A dermoscopic image of a skin lesion — 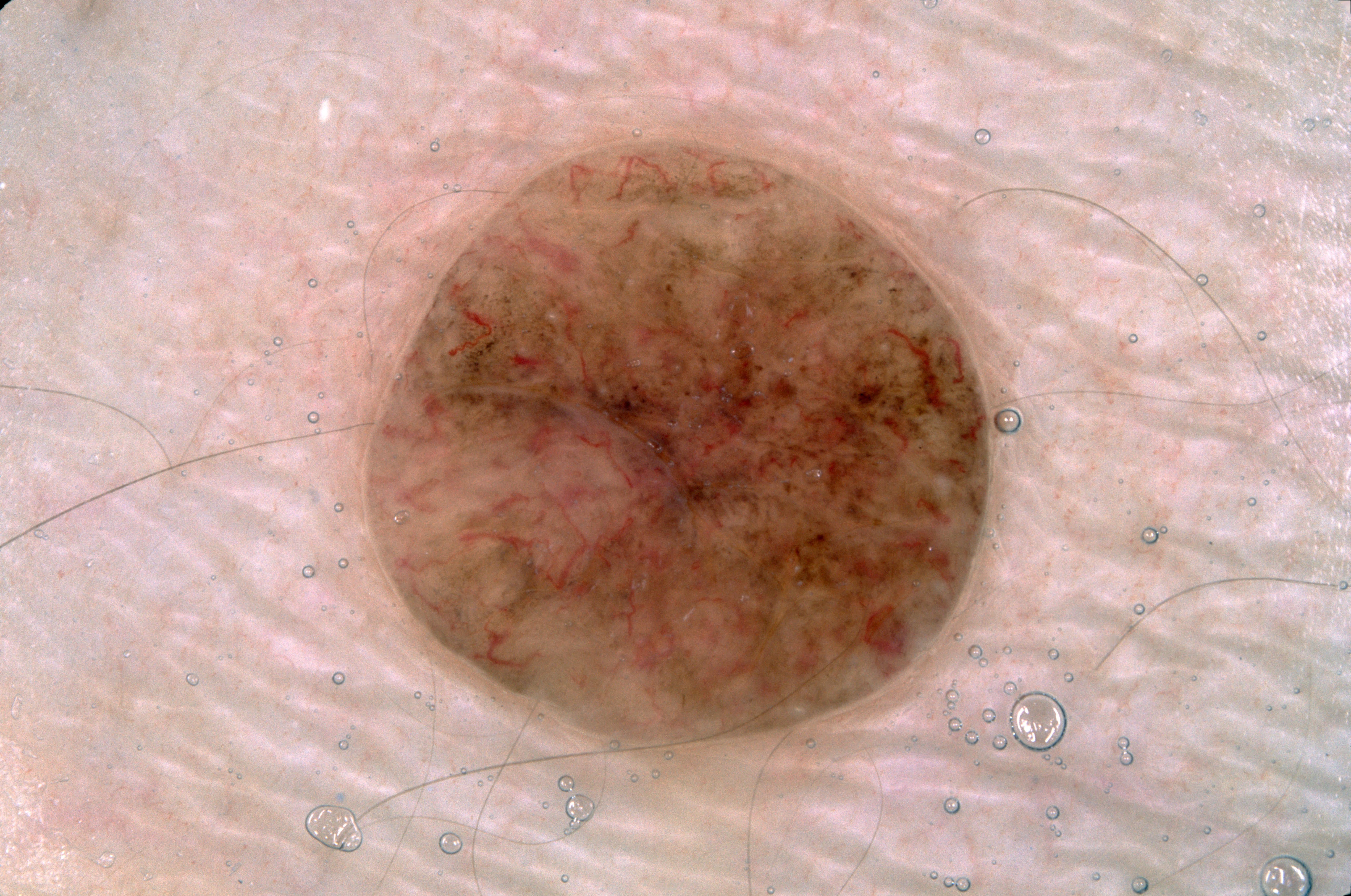The lesion is located at [339, 127, 1017, 790]. The lesion covers approximately 26% of the dermoscopic field. Dermoscopic review identifies milia-like cysts; no streaks, pigment network, or negative network. Consistent with a melanocytic nevus.